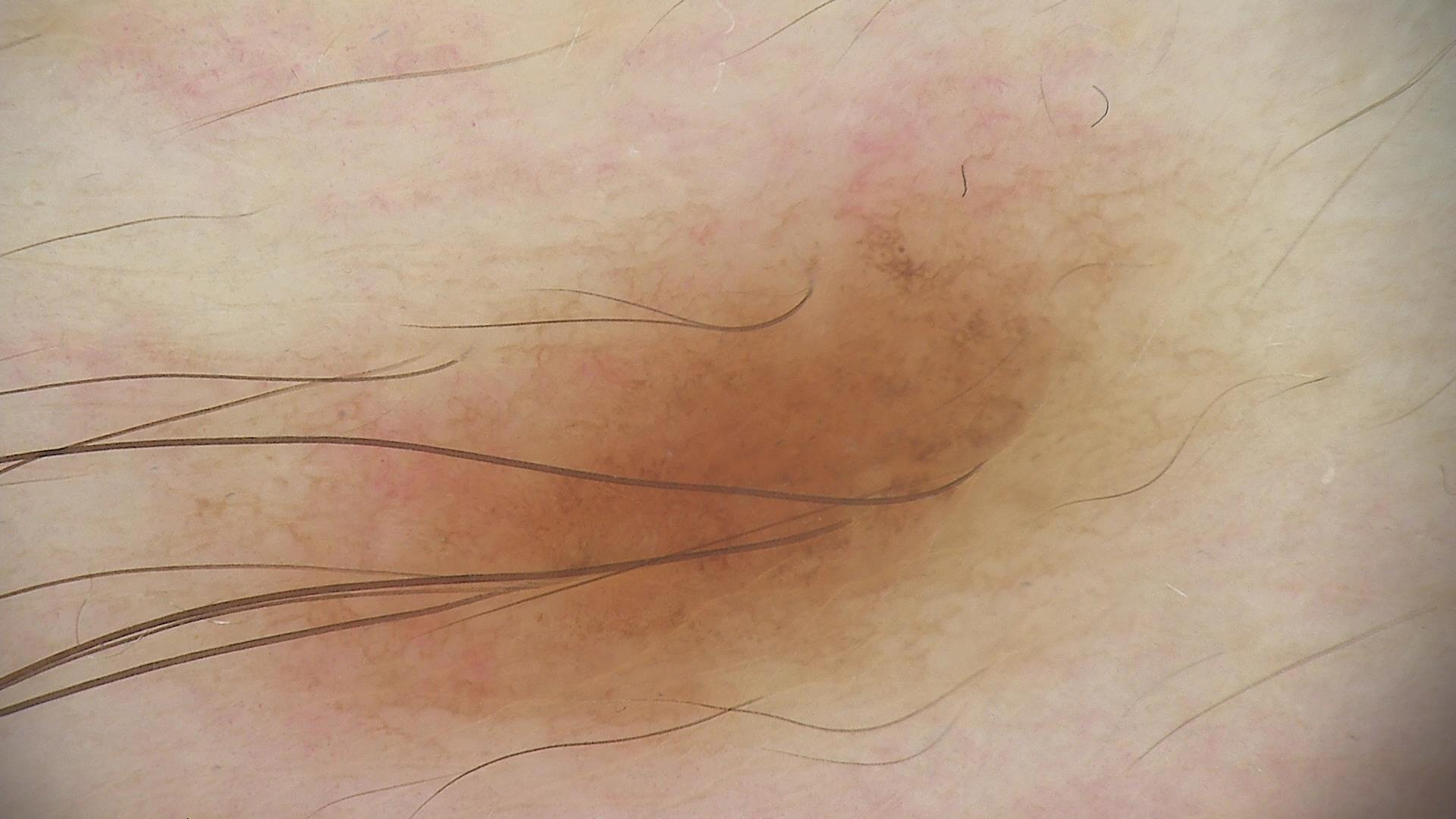diagnosis: compound nevus (expert consensus)